A close-up photograph:
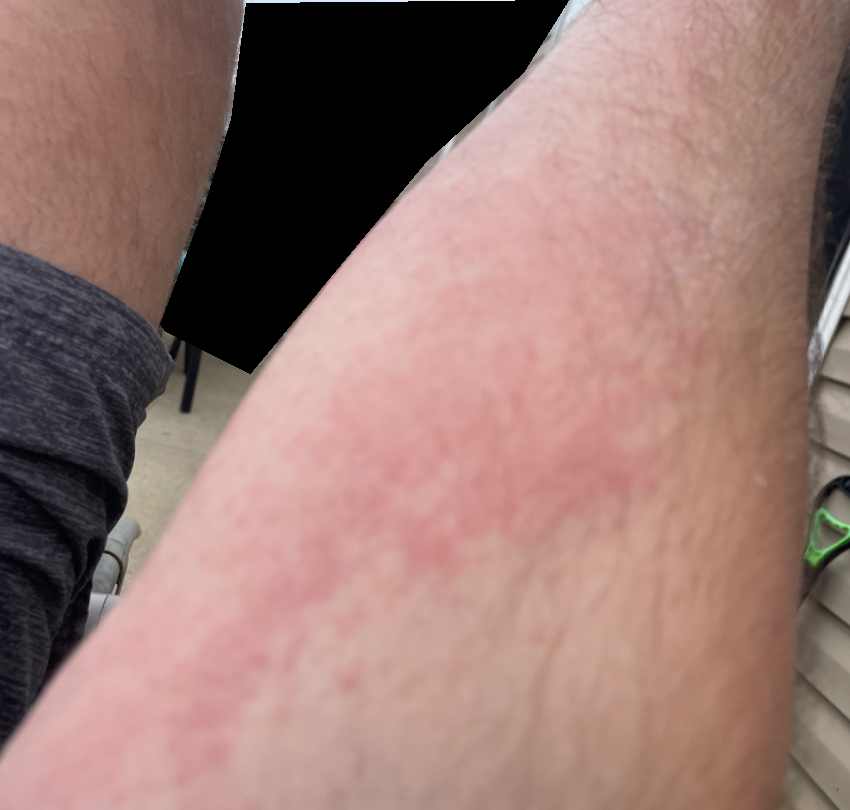Findings:
- assessment — unable to determine